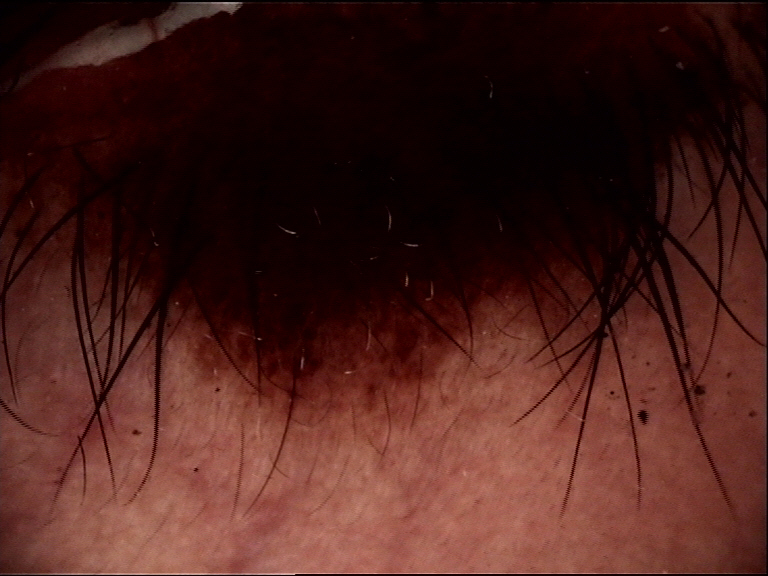Dermoscopy of a skin lesion.
The morphology is that of a banal lesion.
Labeled as a congenital compound nevus.